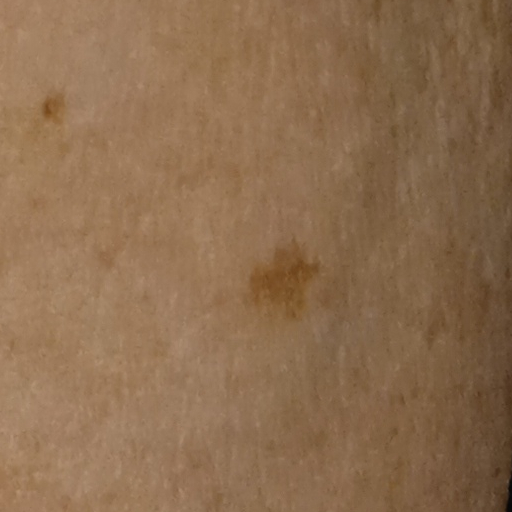Few moles overall by the patient's own estimate. The patient says their skin reddens with sun exposure. The patient reports a personal history of skin cancer and a personal history of cancer. A female patient aged 71. Imaged for a research study, with no referral diagnosis recorded. The lesion is on an arm. The lesion is about 6.1 mm across. The dermatologists' assessment was a melanocytic nevus.